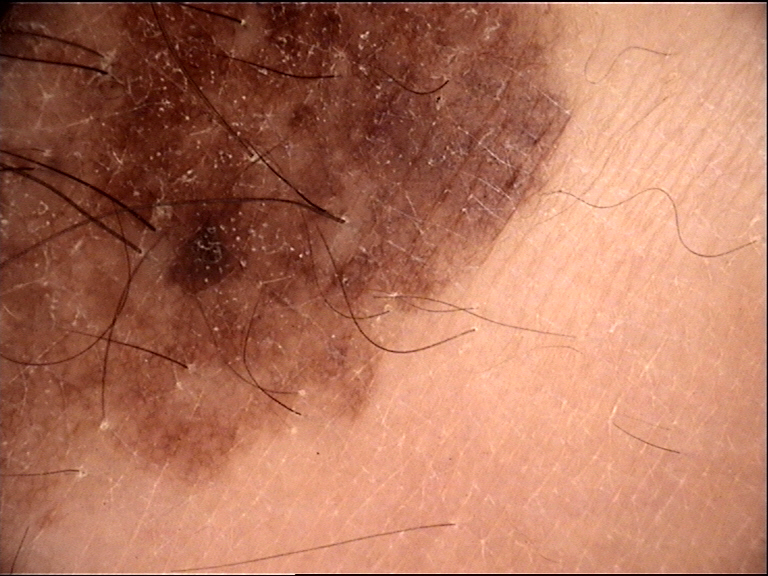A dermoscopy image of a single skin lesion.
The architecture is that of a banal lesion.
Diagnosed as a congenital compound nevus.